The photo was captured at an angle. Female subject, age 50–59.
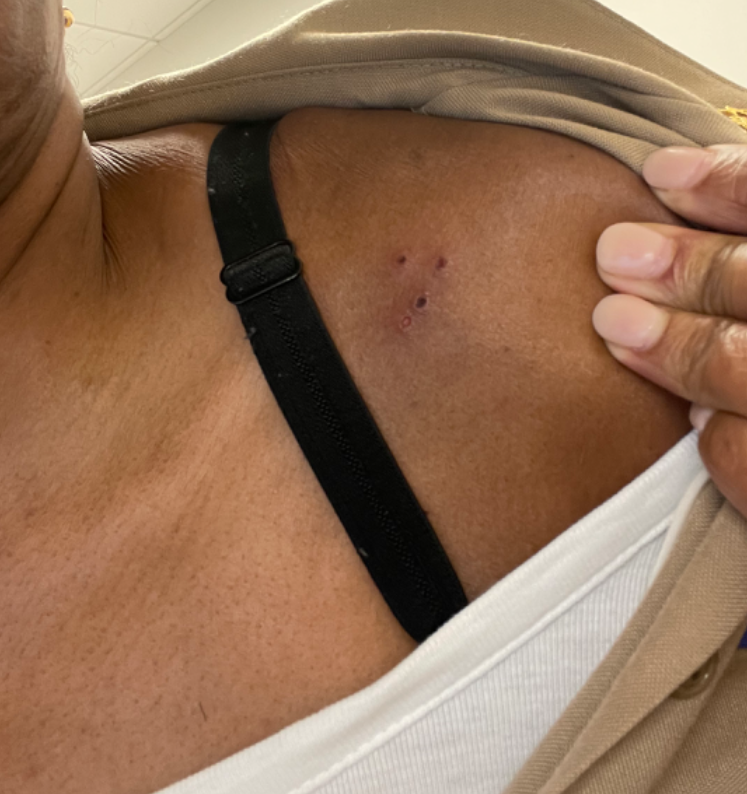The reviewing dermatologist's impression was: Eczema (0.67); Herpes Simplex (0.33).